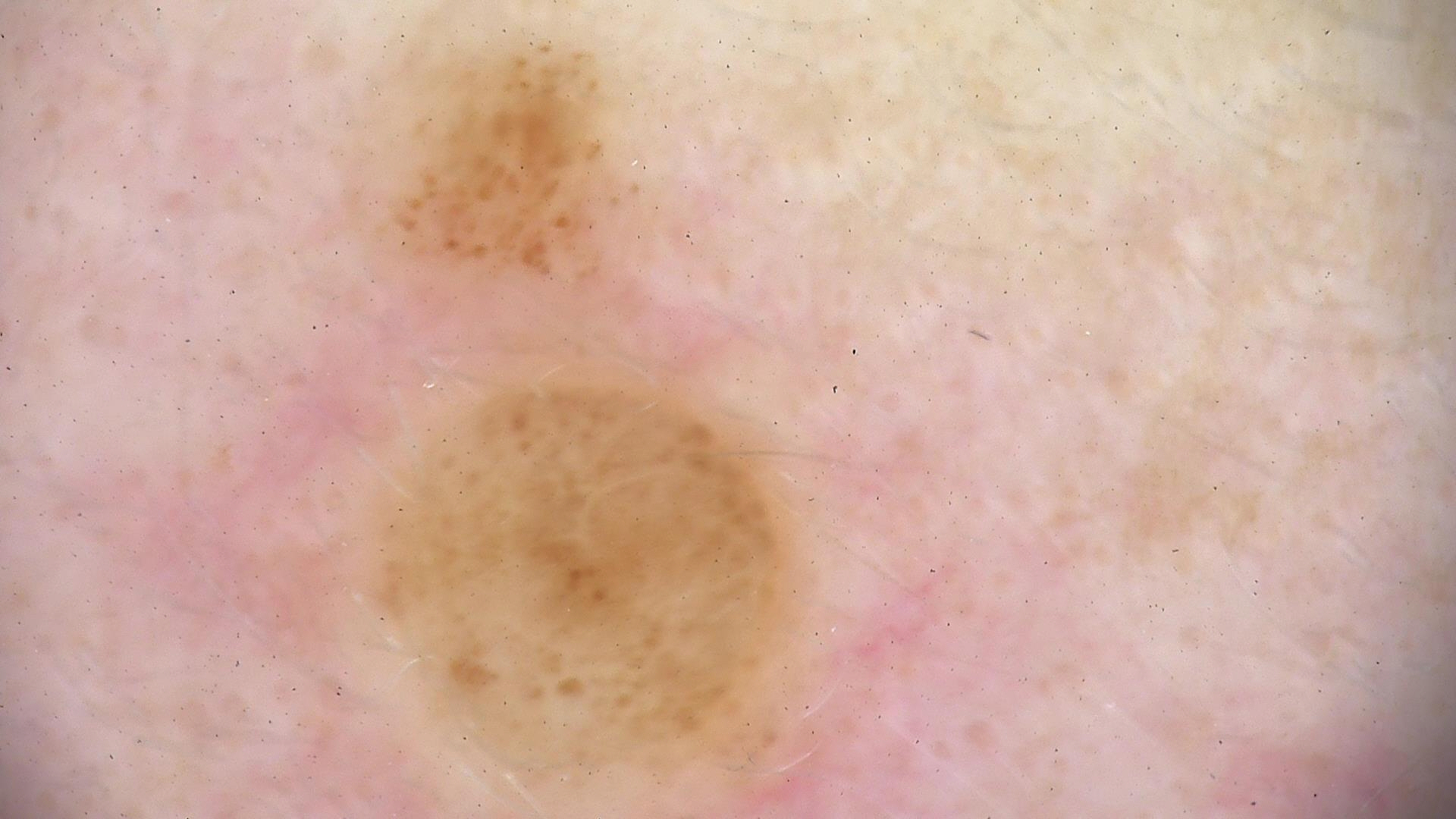Summary: A dermoscopic close-up of a skin lesion. The architecture is that of a banal lesion. Conclusion: The diagnostic label was a dermal nevus.